The photograph was taken at an angle · Fitzpatrick II · the patient is female: 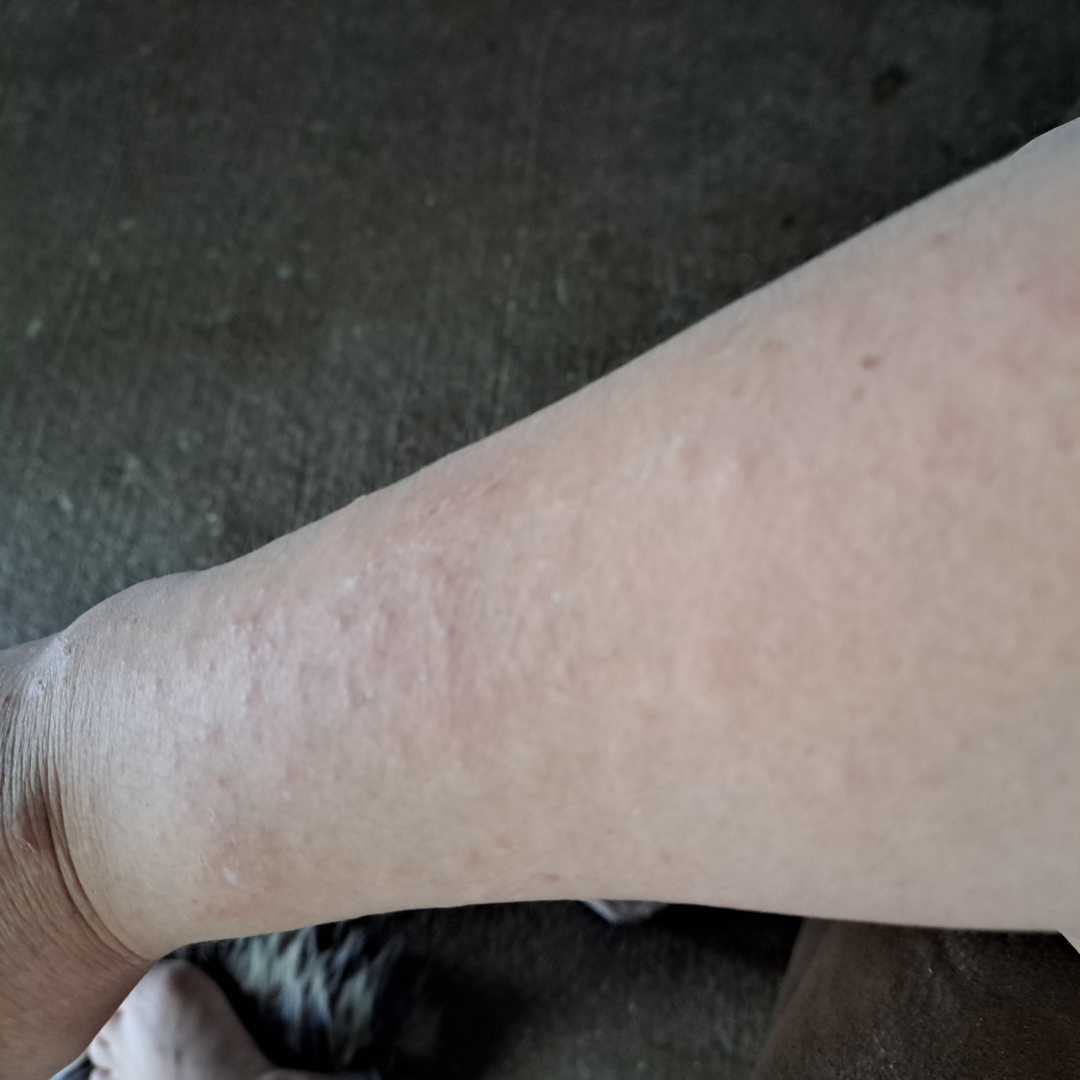Q: What is the dermatologist's impression?
A: the reviewer's impression was Eczema